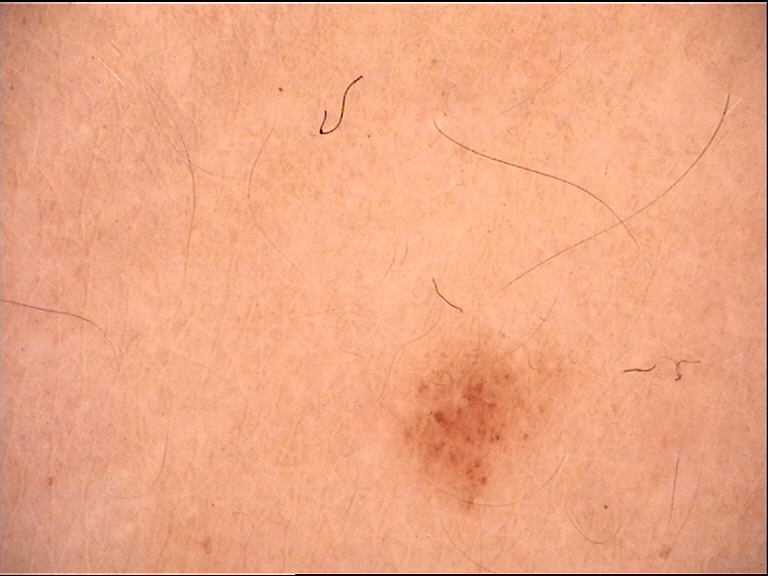Case:
• modality: dermoscopy
• assessment: dysplastic junctional nevus (expert consensus)